A male subject in their late 60s; the chart records prior malignancy (patient or family); recorded as Fitzpatrick II:
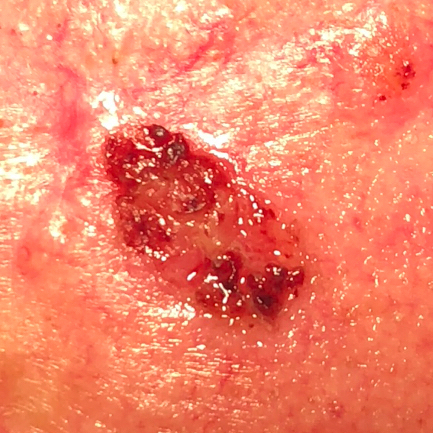{
  "lesion_location": "the face",
  "lesion_size": {
    "diameter_1_mm": 10.0,
    "diameter_2_mm": 4.0
  },
  "symptoms": {
    "present": [
      "itching",
      "elevation",
      "bleeding",
      "pain",
      "growth"
    ]
  },
  "diagnosis": {
    "name": "basal cell carcinoma",
    "code": "BCC",
    "malignancy": "malignant",
    "confirmation": "histopathology"
  }
}